No constitutional symptoms were reported; Fitzpatrick skin type III; the arm, leg and back of the hand are involved; the patient described the issue as a rash; close-up view; the patient indicates the lesion is raised or bumpy; reported lesion symptoms include itching and burning; the patient indicates the condition has been present for more than one year; the patient is female.
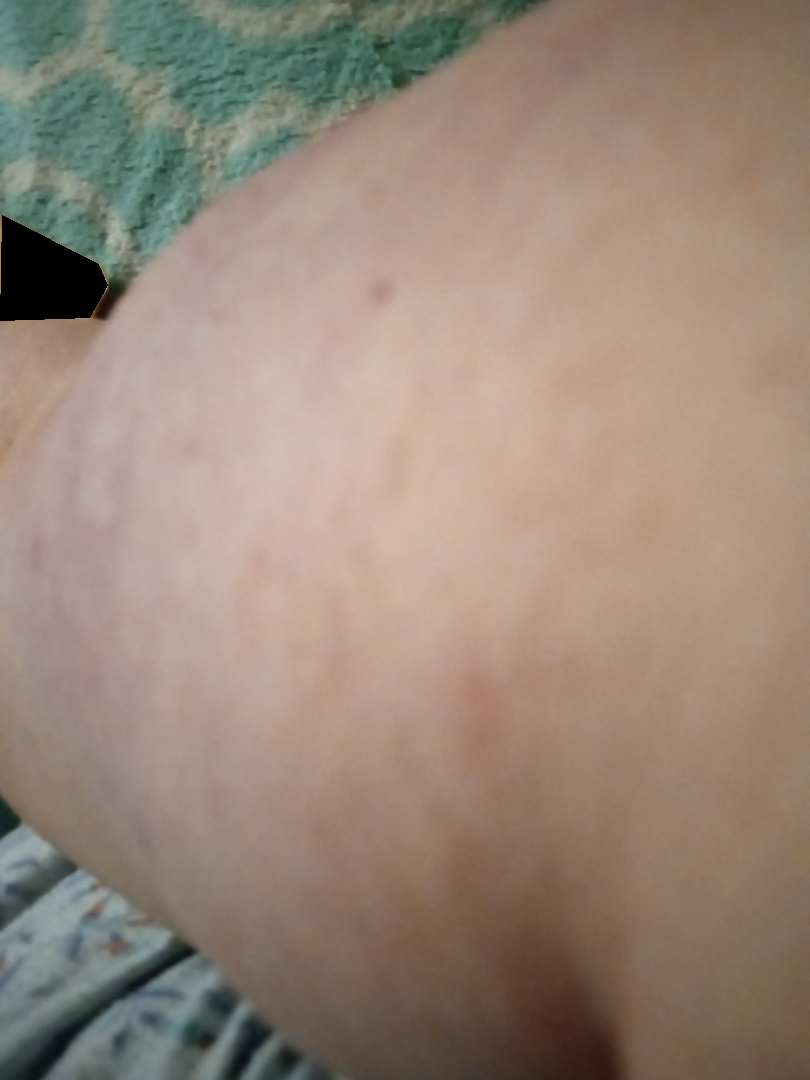The case was indeterminate on photographic review.